A dermoscopic image of a skin lesion.
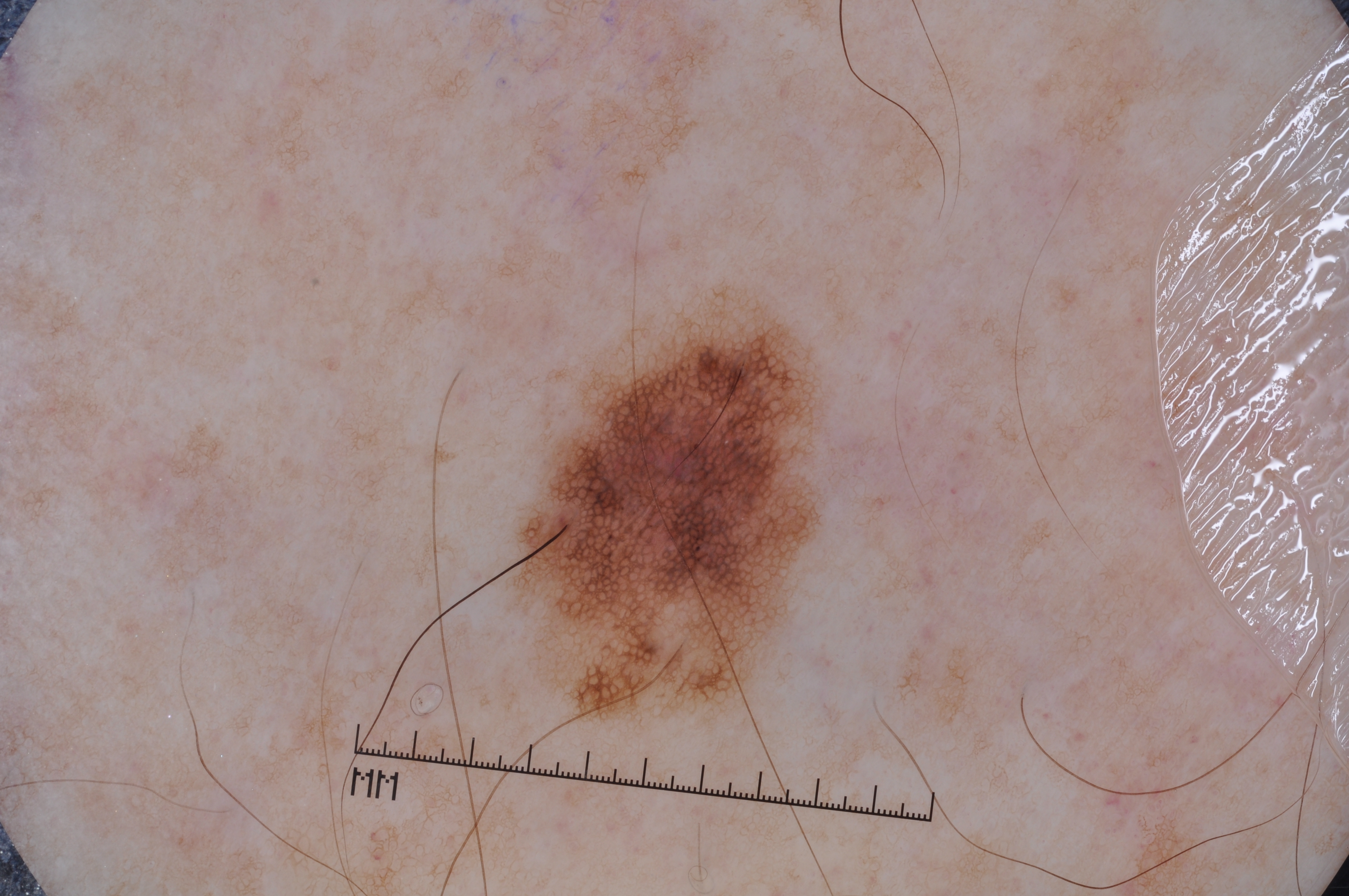{
  "lesion_location": {
    "bbox_xyxy": [
      527,
      309,
      811,
      707
    ]
  },
  "diagnosis": {
    "name": "melanocytic nevus",
    "malignancy": "benign",
    "lineage": "melanocytic",
    "provenance": "clinical"
  }
}